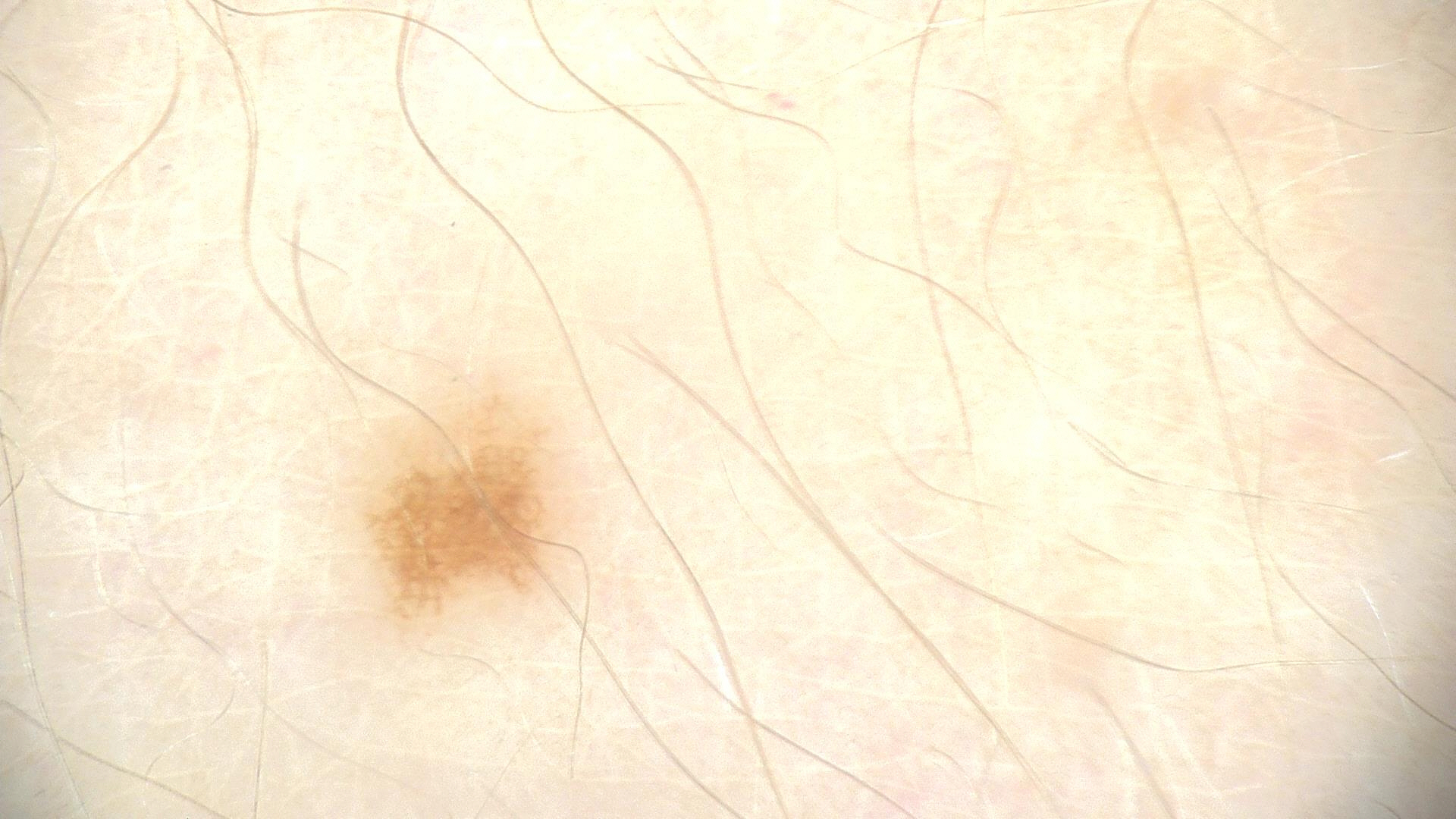Consistent with a dysplastic junctional nevus.